The lesion involves the top or side of the foot; the photo was captured at an angle:
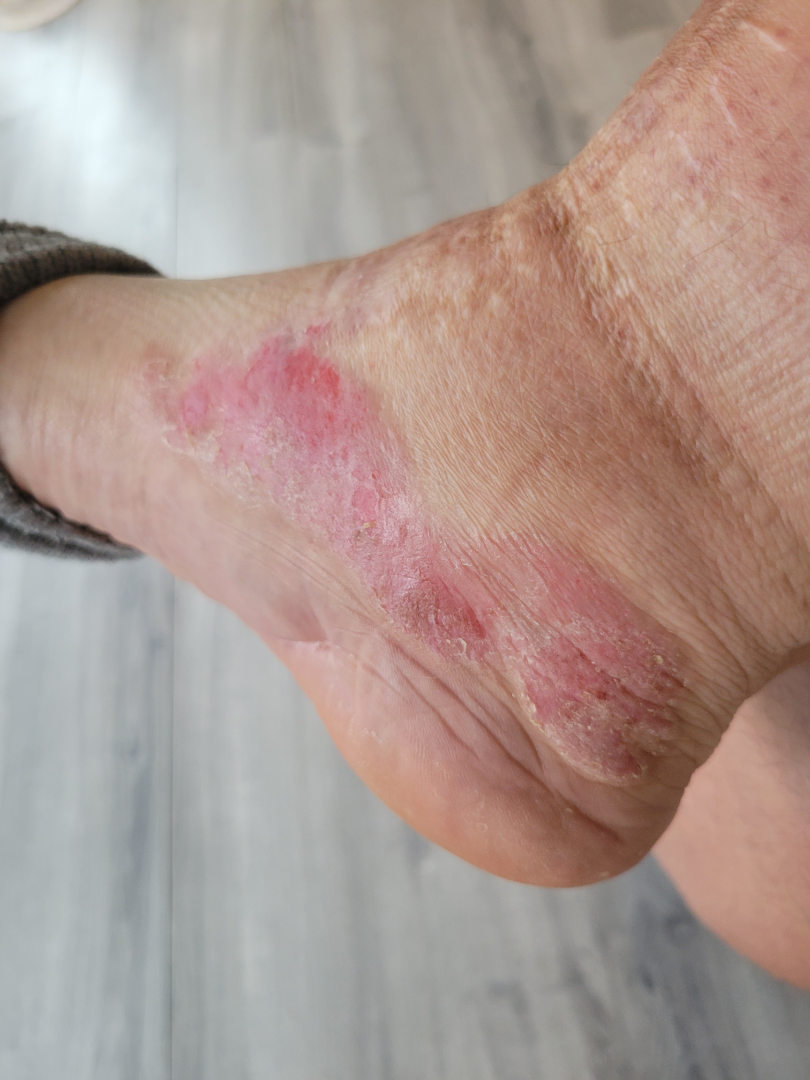impression = most consistent with Cutaneous T Cell Lymphoma; also consider Tinea; an alternative is Irritant Contact Dermatitis.